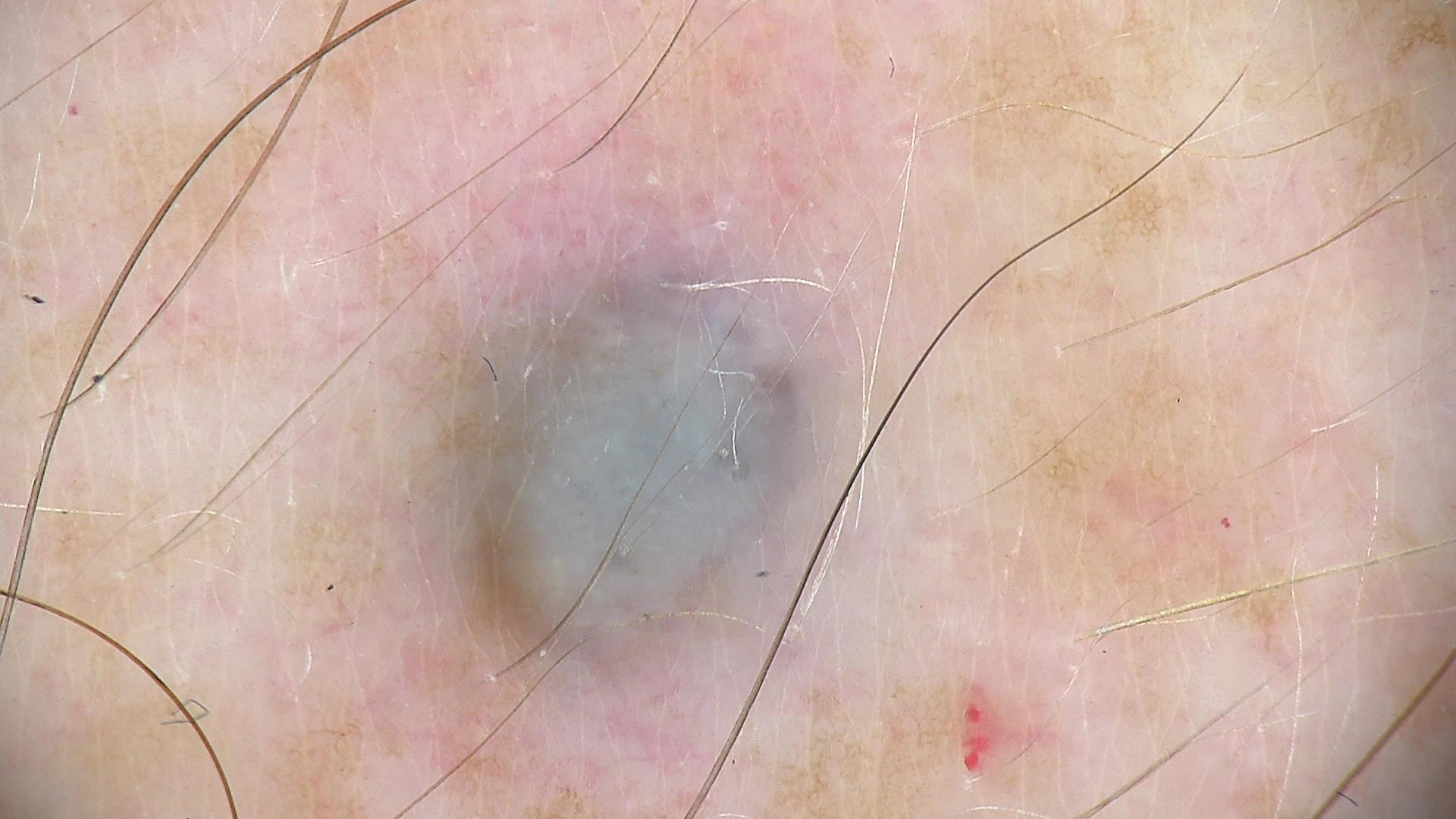Findings: A dermatoscopic image of a skin lesion. The morphology is that of a dermal, banal lesion. Impression: The diagnostic label was a blue nevus.